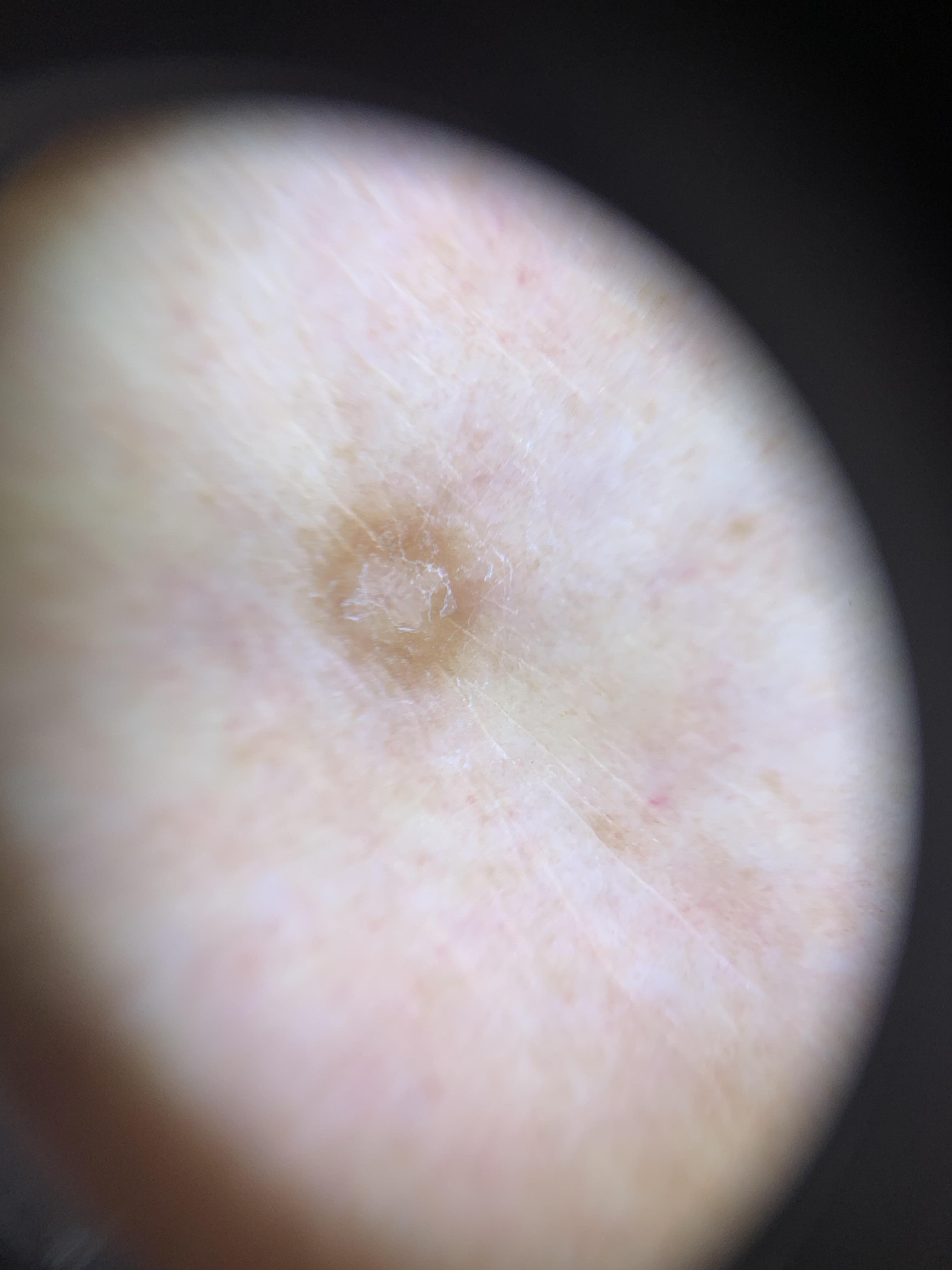  image: dermoscopic image
  patient:
    age_approx: 75
    sex: male
  skin_type: III
  lesion_location:
    region: a lower extremity
  diagnosis:
    name: Dermatofibroma
    malignancy: benign
    confirmation: expert clinical impression
    lineage: fibro-histiocytic